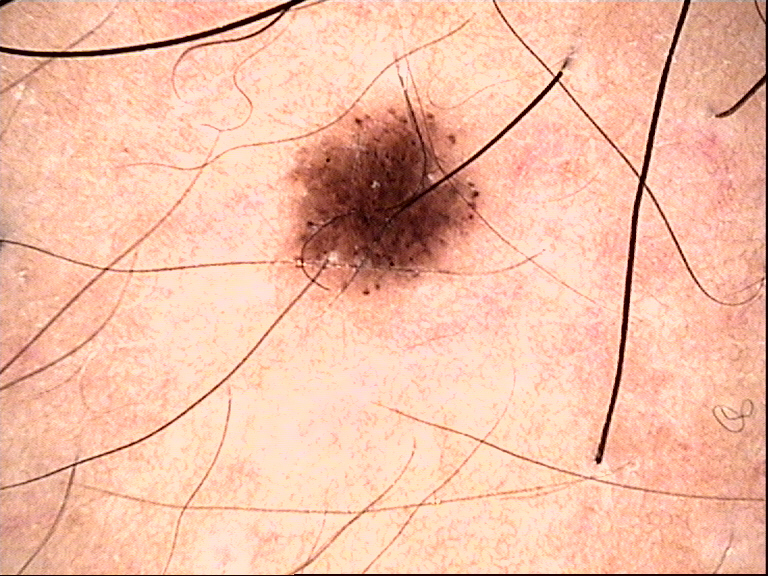* diagnosis: dysplastic junctional nevus (expert consensus)